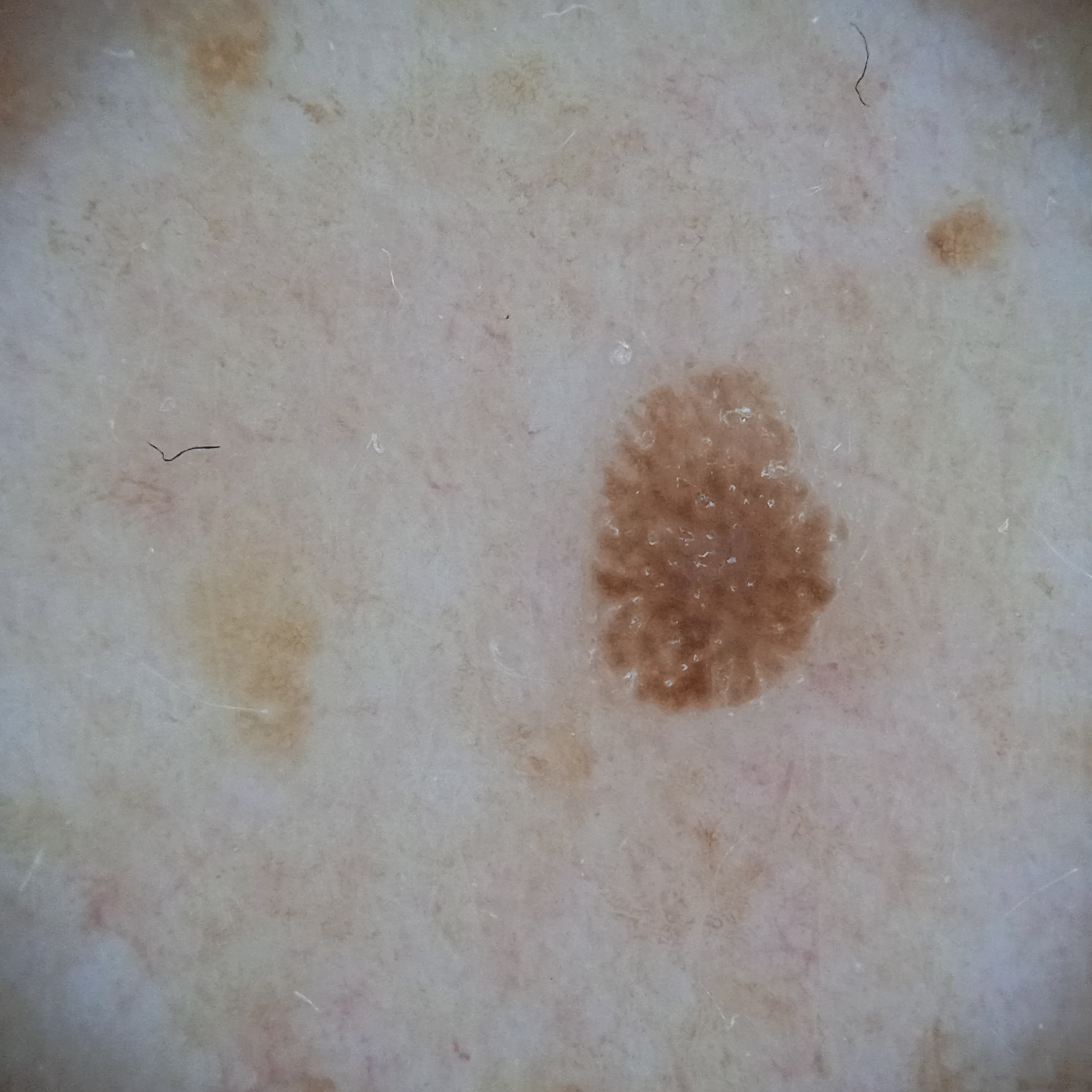- imaging: dermoscopy
- referral: research study (no referral diagnosis)
- nevus count: few melanocytic nevi overall
- patient: male, 62 years of age
- risk factors: no prior organ transplant
- sun reaction: skin reddens with sun exposure
- anatomic site: the back
- size: 4.3 mm
- assessment: seborrheic keratosis (dermatologist consensus)